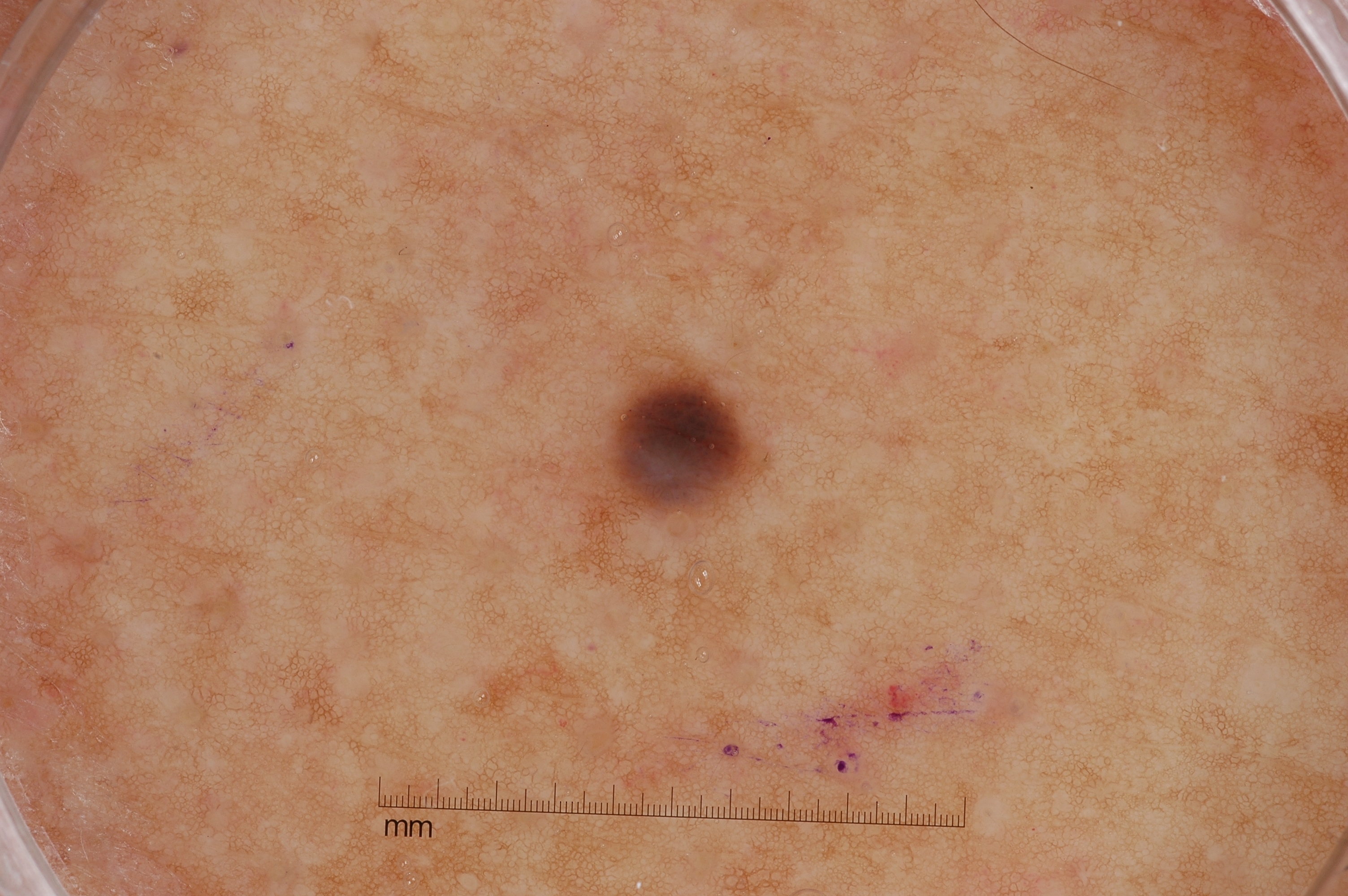A dermatoscopic image of a skin lesion.
The subject is a male aged around 70.
Dermoscopically, the lesion shows no streaks, milia-like cysts, negative network, or pigment network.
The lesion spans 606, 365, 755, 518.
Expert review diagnosed this as a melanocytic nevus.